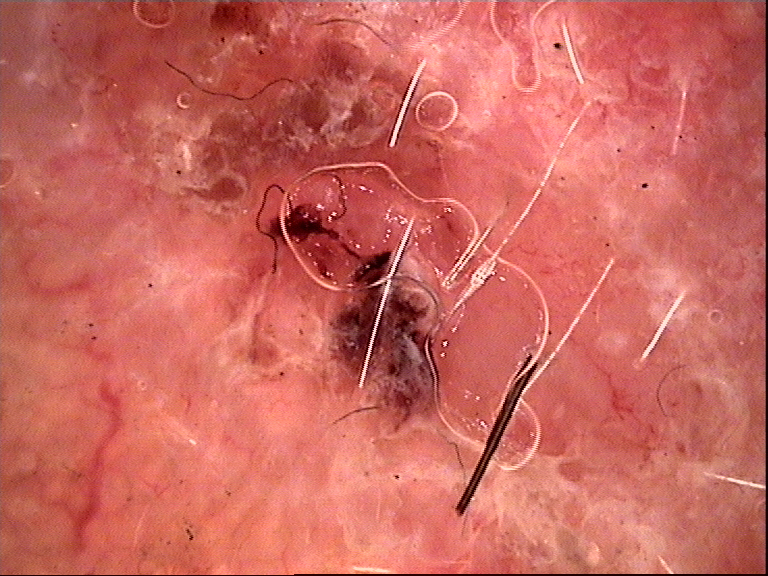The biopsy diagnosis was a basal cell carcinoma.